A dermoscopy image of a single skin lesion: 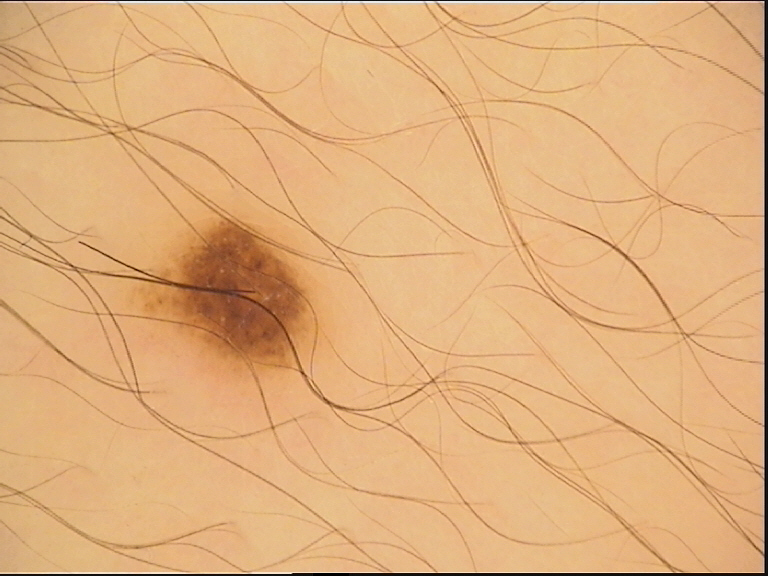The diagnostic label was a dysplastic junctional nevus.